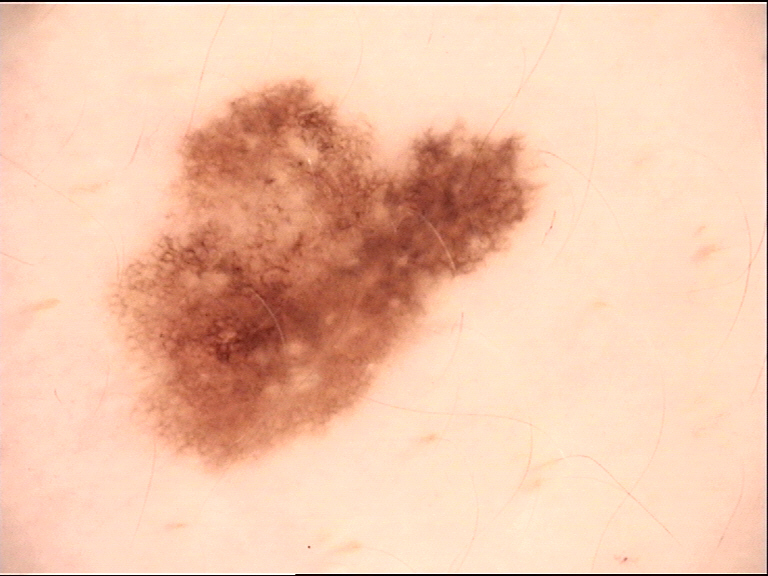Labeled as a dysplastic junctional nevus.